A clinical photo of a skin lesion taken with a smartphone · a female patient in their 70s · the patient was assessed as Fitzpatrick skin type II: 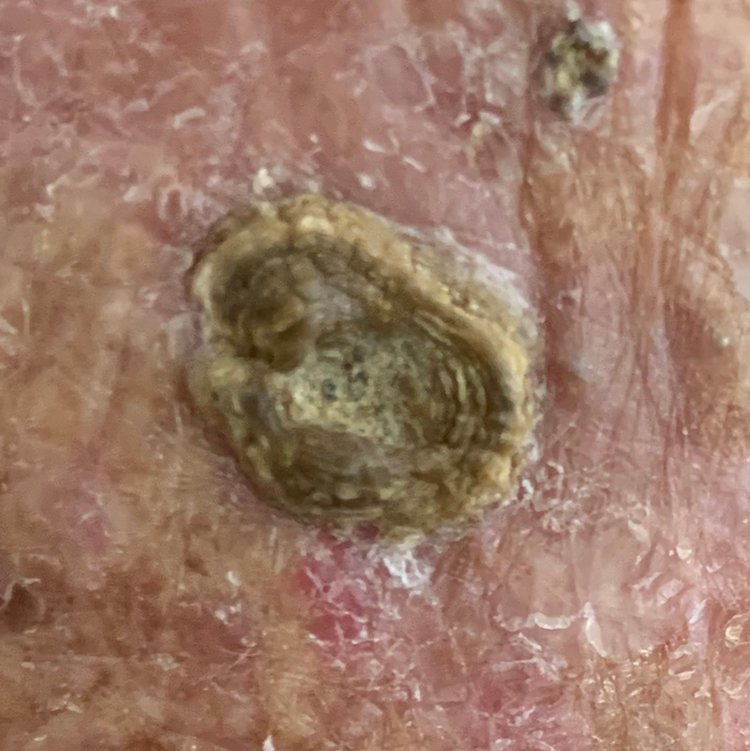Notes:
– region — an arm
– lesion size — 10 × 9 mm
– symptoms — elevation, pain, itching
– diagnostic label — actinic keratosis (biopsy-proven)